Reported duration is less than one week. The photo was captured at an angle. FST V; human graders estimated MST 6–7. The lesion is described as raised or bumpy. The patient described the issue as a rash. The leg, arm and front of the torso are involved. The lesion is associated with itching: 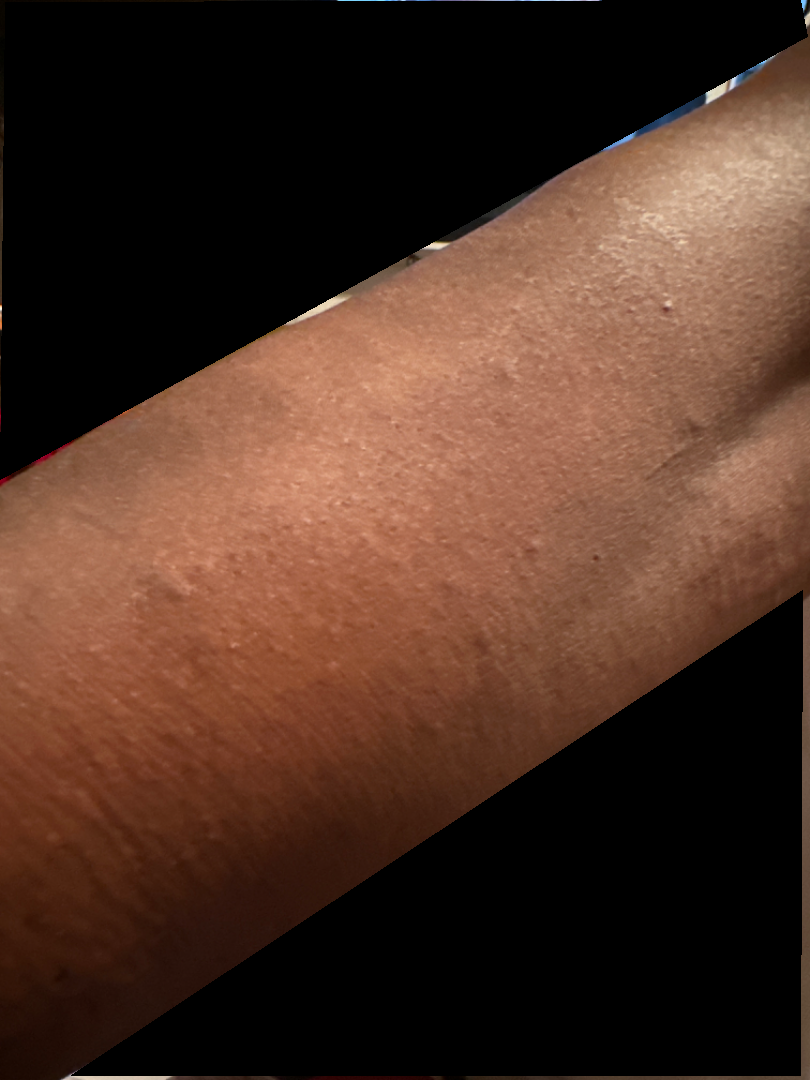The reviewing dermatologist was unable to assign a differential diagnosis from the image.